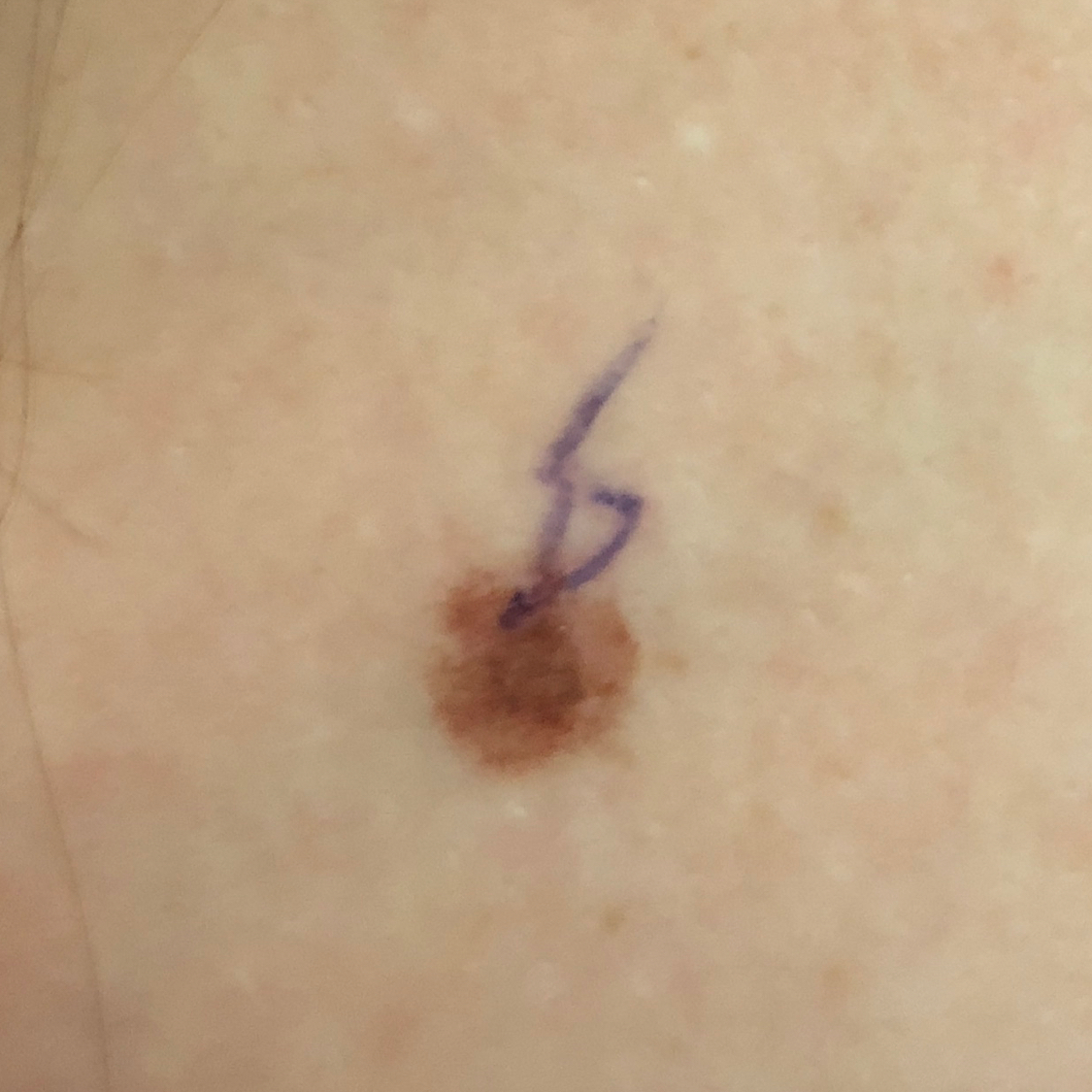Findings:
- impression — nevus (clinical consensus)